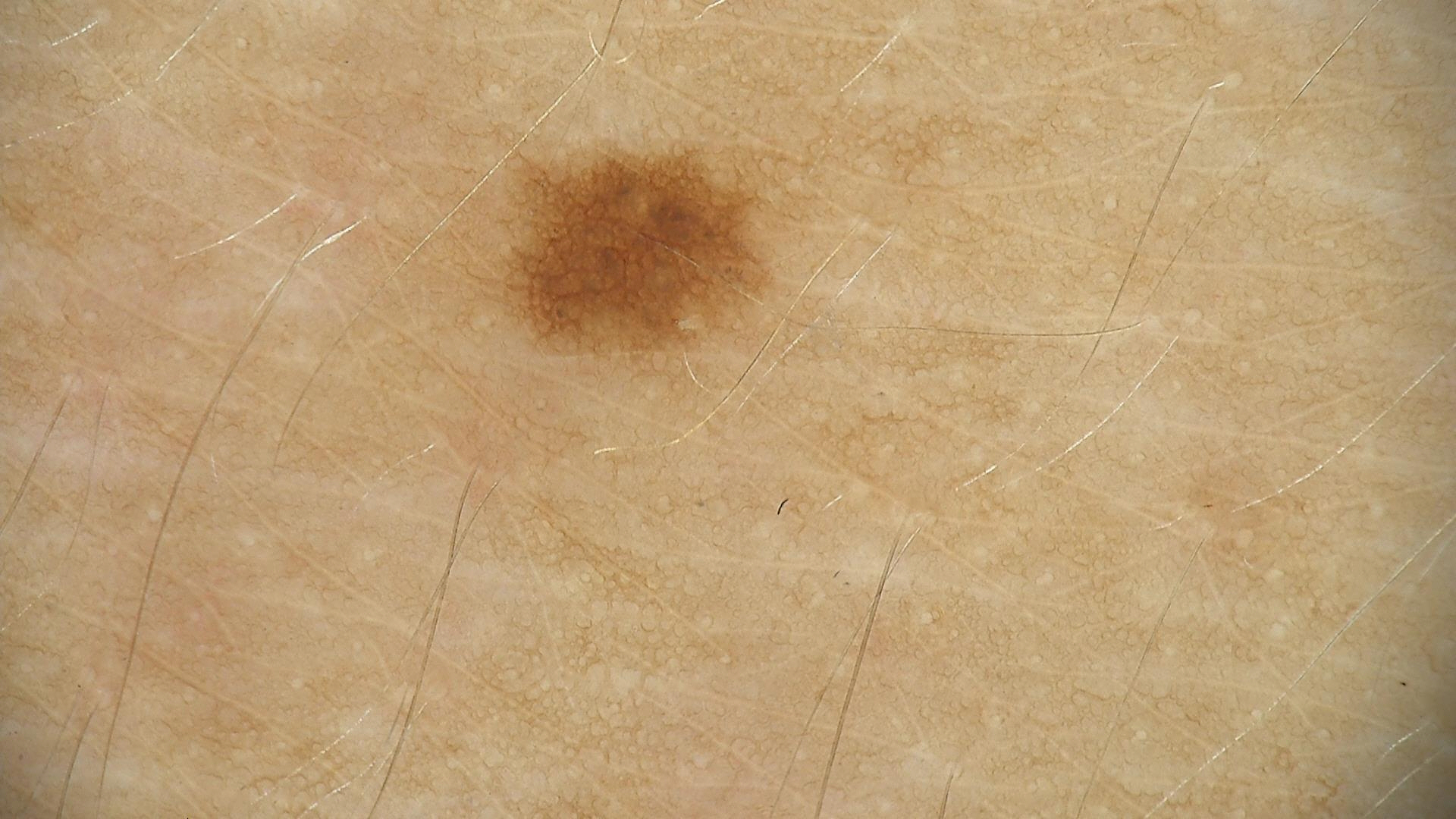Conclusion: The diagnosis was a junctional nevus.